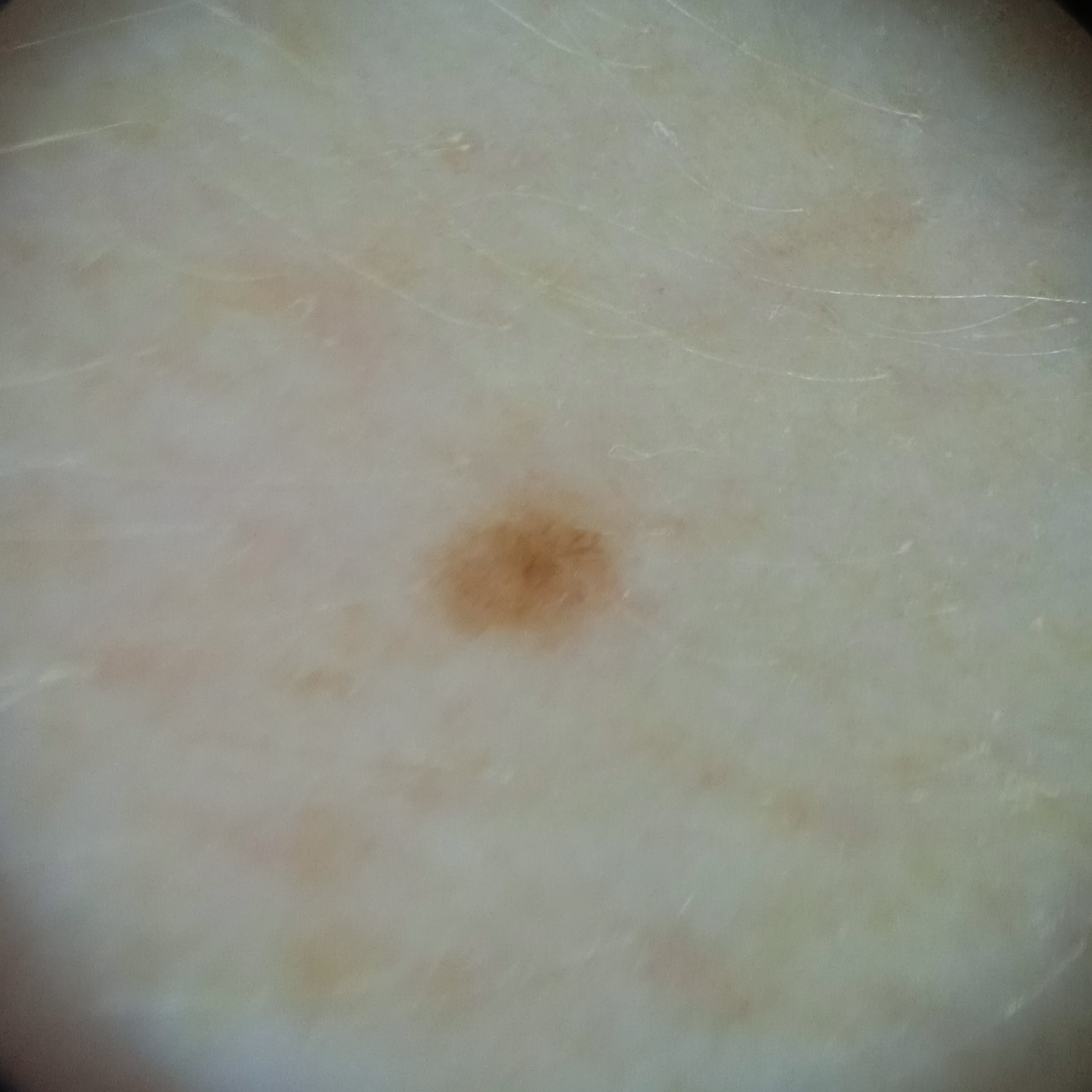A moderate number of moles by the patient's own estimate. The patient says their skin reddens painfully with sun exposure. A dermatoscopic image of a skin lesion. A female subject 50 years of age. Collected as part of a research study, without a referral diagnosis. The lesion involves an arm. The lesion measures approximately 2 mm. Dermatologist review favored a melanocytic nevus.